A dermatoscopic image of a skin lesion · a female subject, approximately 45 years of age — 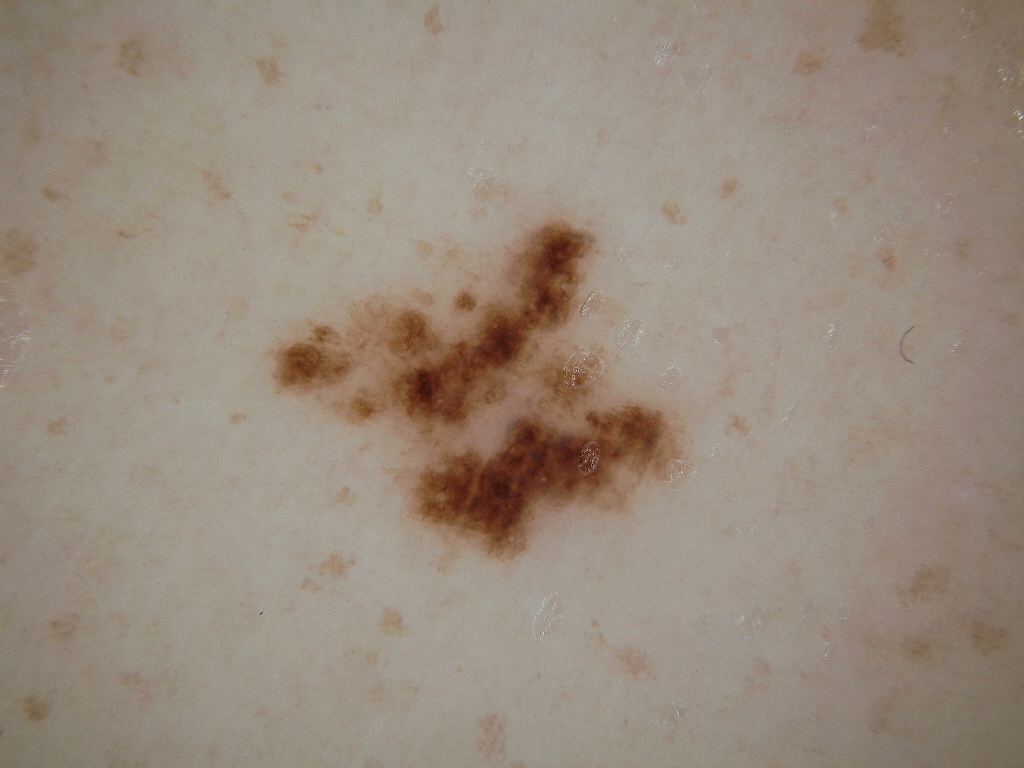dermoscopic_features:
  present:
    - milia-like cysts
    - pigment network
  absent:
    - negative network
    - globules
    - streaks
lesion_location:
  bbox_xyxy:
    - 246
    - 202
    - 701
    - 574
diagnosis:
  name: melanocytic nevus
  malignancy: benign
  lineage: melanocytic
  provenance: clinical